A close-up photograph; located on the arm and leg: 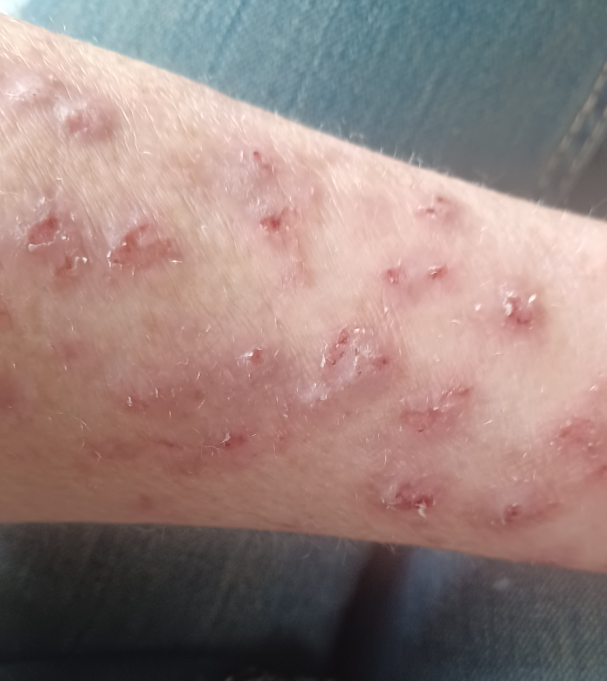On teledermatology review, most consistent with Inflicted skin lesions; the differential also includes Eczema; a more distant consideration is Allergic Contact Dermatitis.